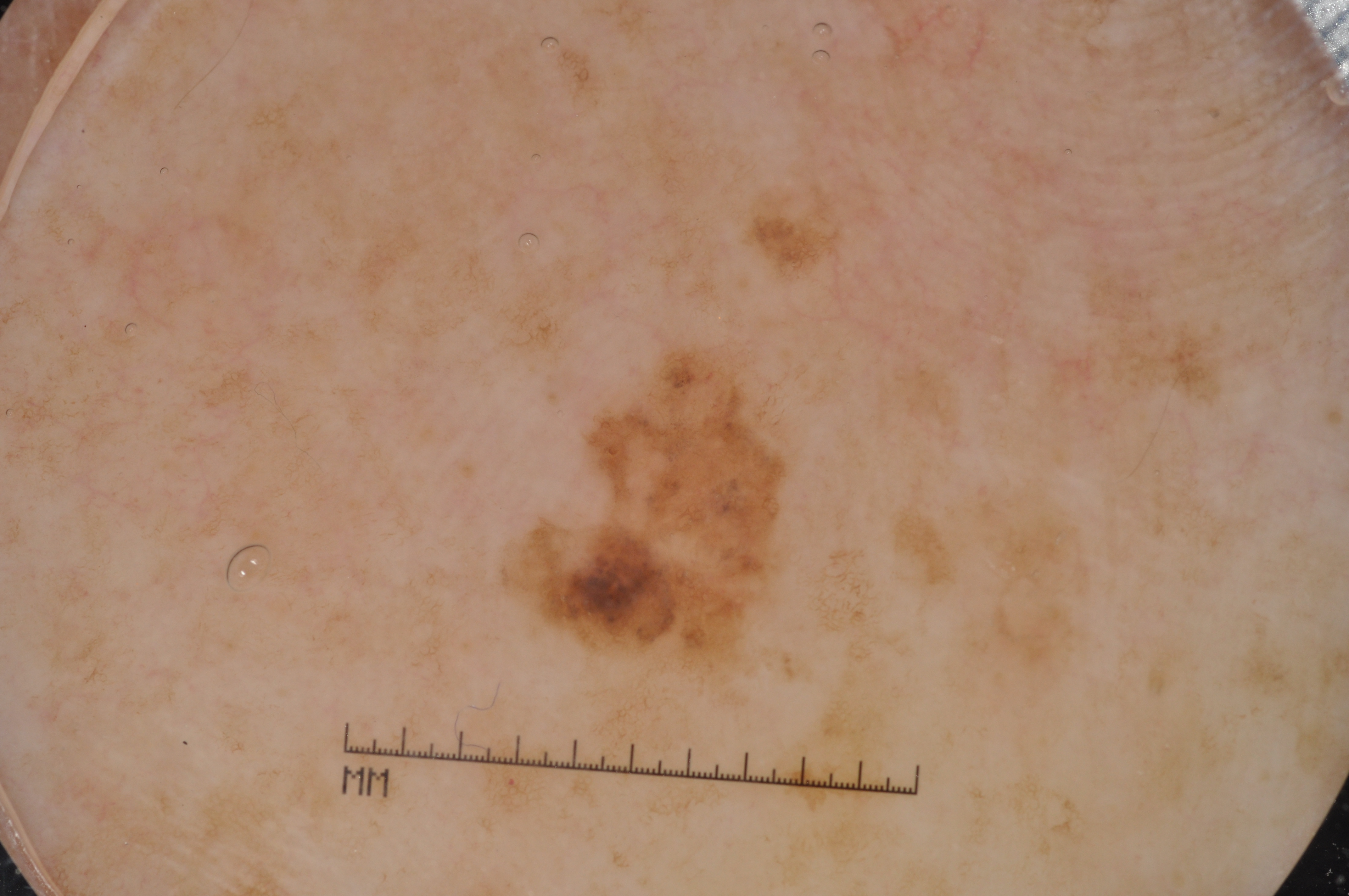Q: What is the imaging modality?
A: dermoscopy of a skin lesion
Q: Patient demographics?
A: male, aged 73-77
Q: What is the lesion's bounding box?
A: <box>517, 357, 780, 658</box>
Q: Lesion extent?
A: ~4% of the field
Q: What dermoscopic features are present?
A: pigment network; absent: streaks, negative network, and milia-like cysts
Q: What is this lesion?
A: a melanoma